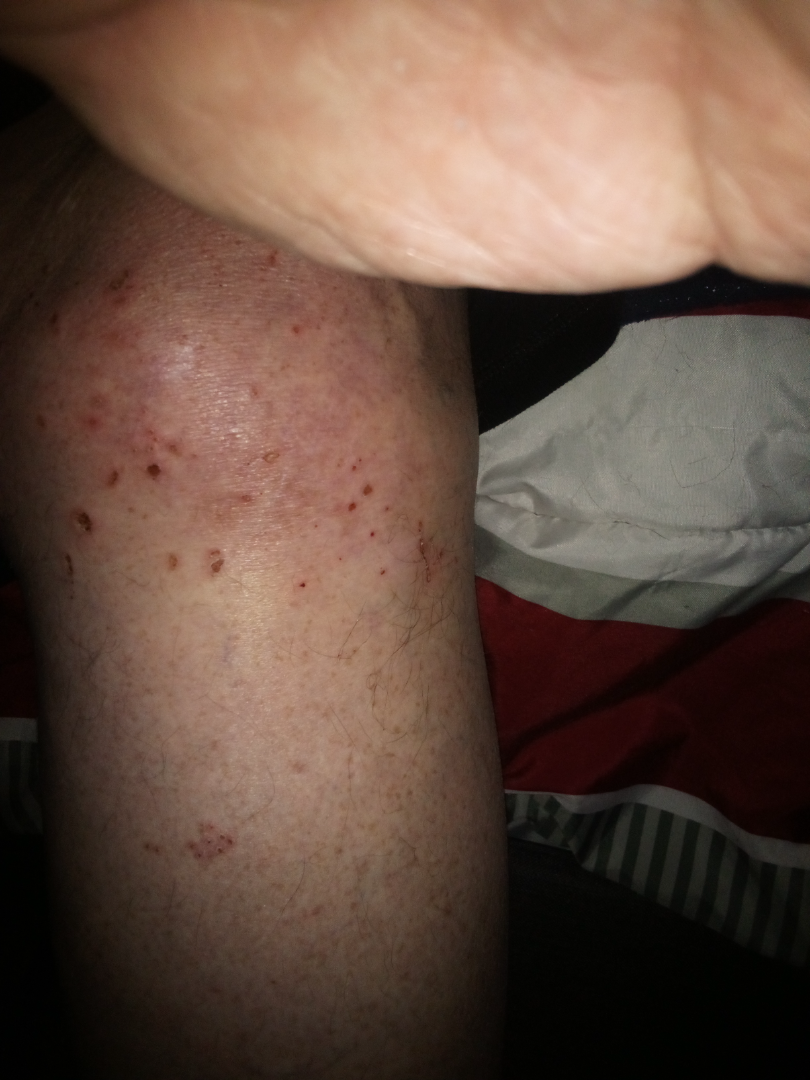The case was difficult to assess from the available photograph. An image taken at a distance. The leg is involved. Texture is reported as fluid-filled. Skin tone: FST II. The subject is 50–59, male. The patient described the issue as a rash.